The subject is a male aged 40–49; the lesion is associated with itching; the lesion involves the arm; the photo was captured at a distance; texture is reported as raised or bumpy; the patient considered this a rash: 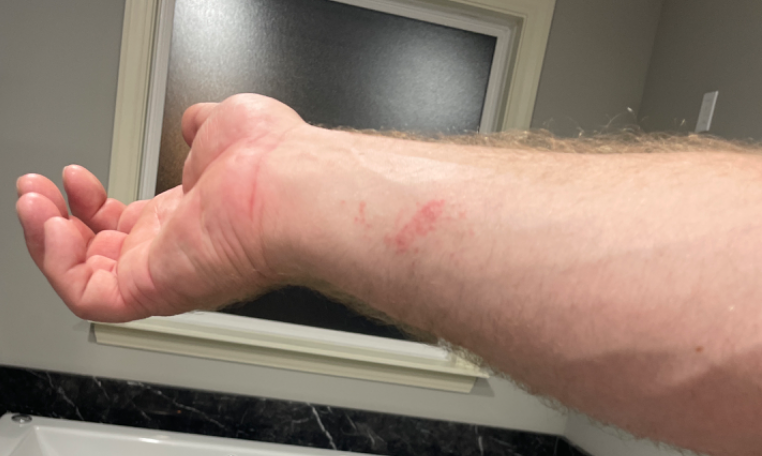Q: Could the case be diagnosed?
A: indeterminate from the photograph